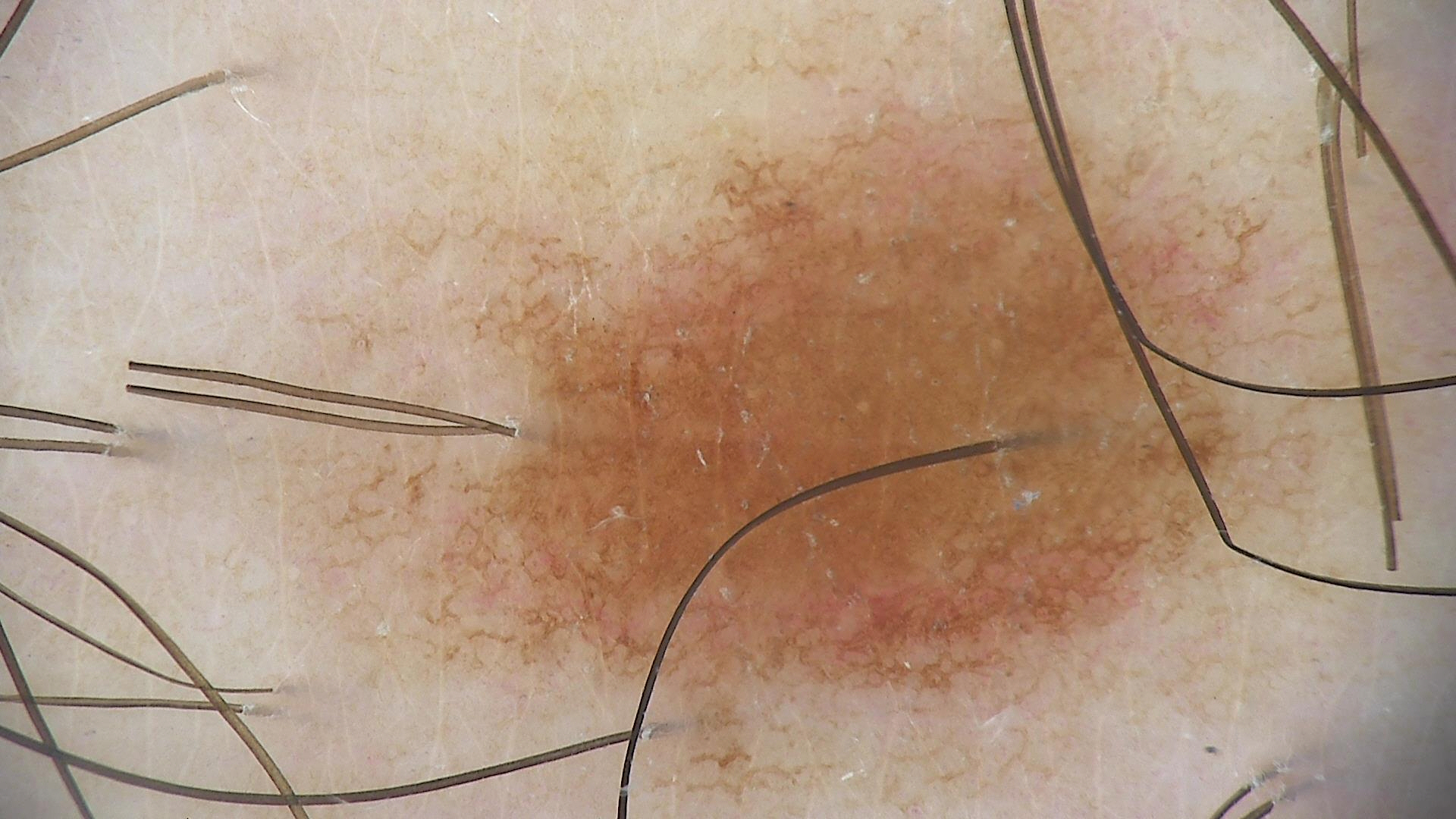Q: What is the imaging modality?
A: dermatoscopy
Q: What is the diagnosis?
A: dysplastic junctional nevus (expert consensus)